A dermoscopy image of a single skin lesion:
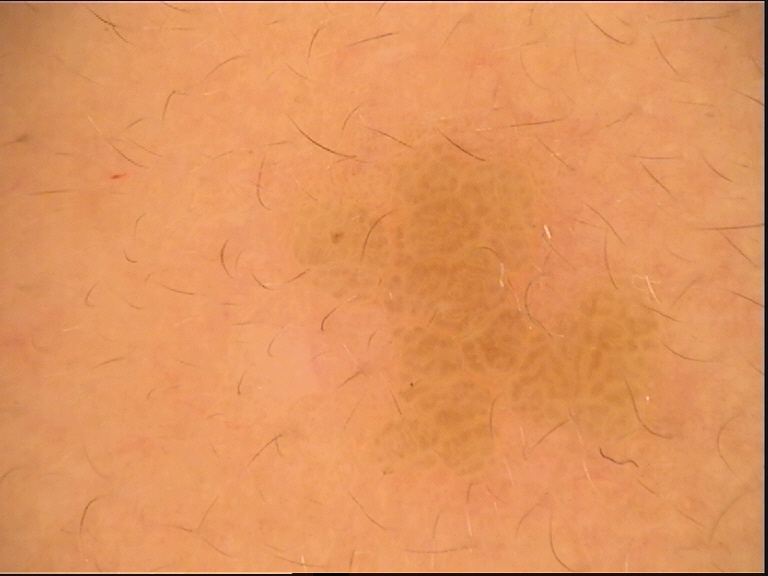The architecture is that of a keratinocytic lesion.
Diagnosed as a seborrheic keratosis.